Lay graders estimated Monk Skin Tone 1 or 2 (two reviewer pools); the contributor reports the condition has been present for one to four weeks; self-categorized by the patient as a rash; associated systemic symptoms include fatigue and joint pain; the photograph is a close-up of the affected area; the top or side of the foot and leg are involved; female patient, age 30–39; the contributor reports enlargement, darkening, itching, pain and burning — 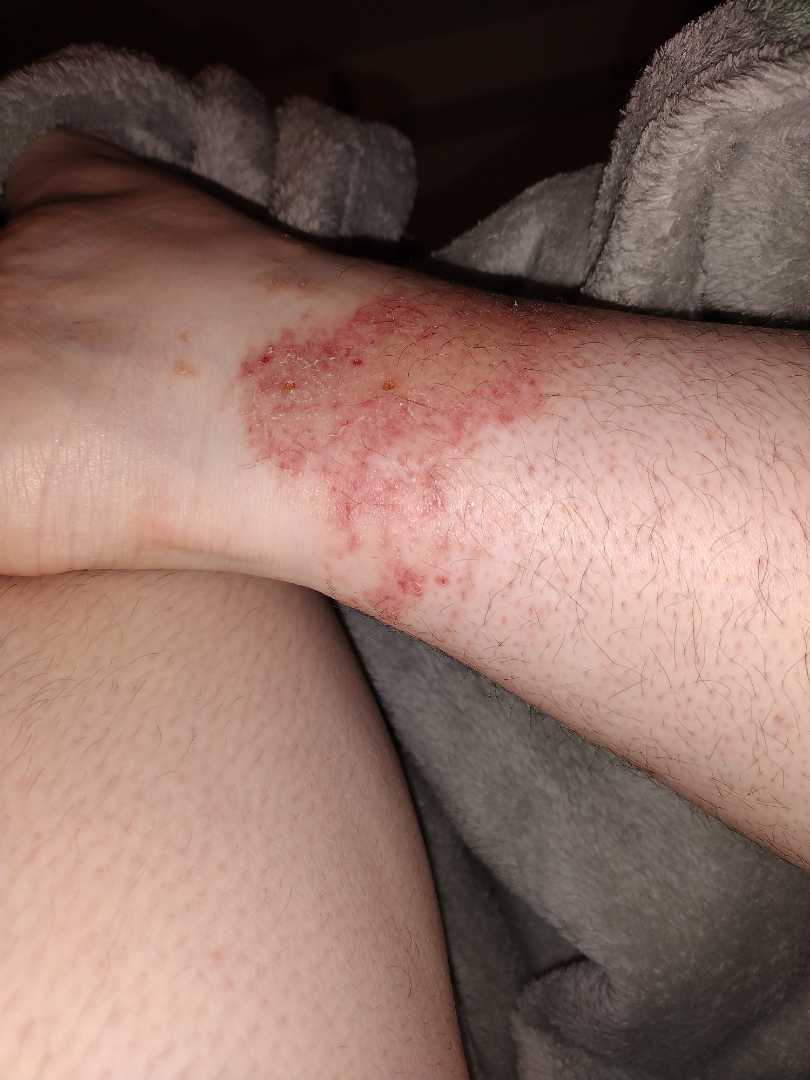Allergic Contact Dermatitis and Stasis Dermatitis were considered with similar weight; possibly Eczema; less probable is Irritant Contact Dermatitis; lower on the differential is Contact dermatitis.